A dermoscopic image of a skin lesion: 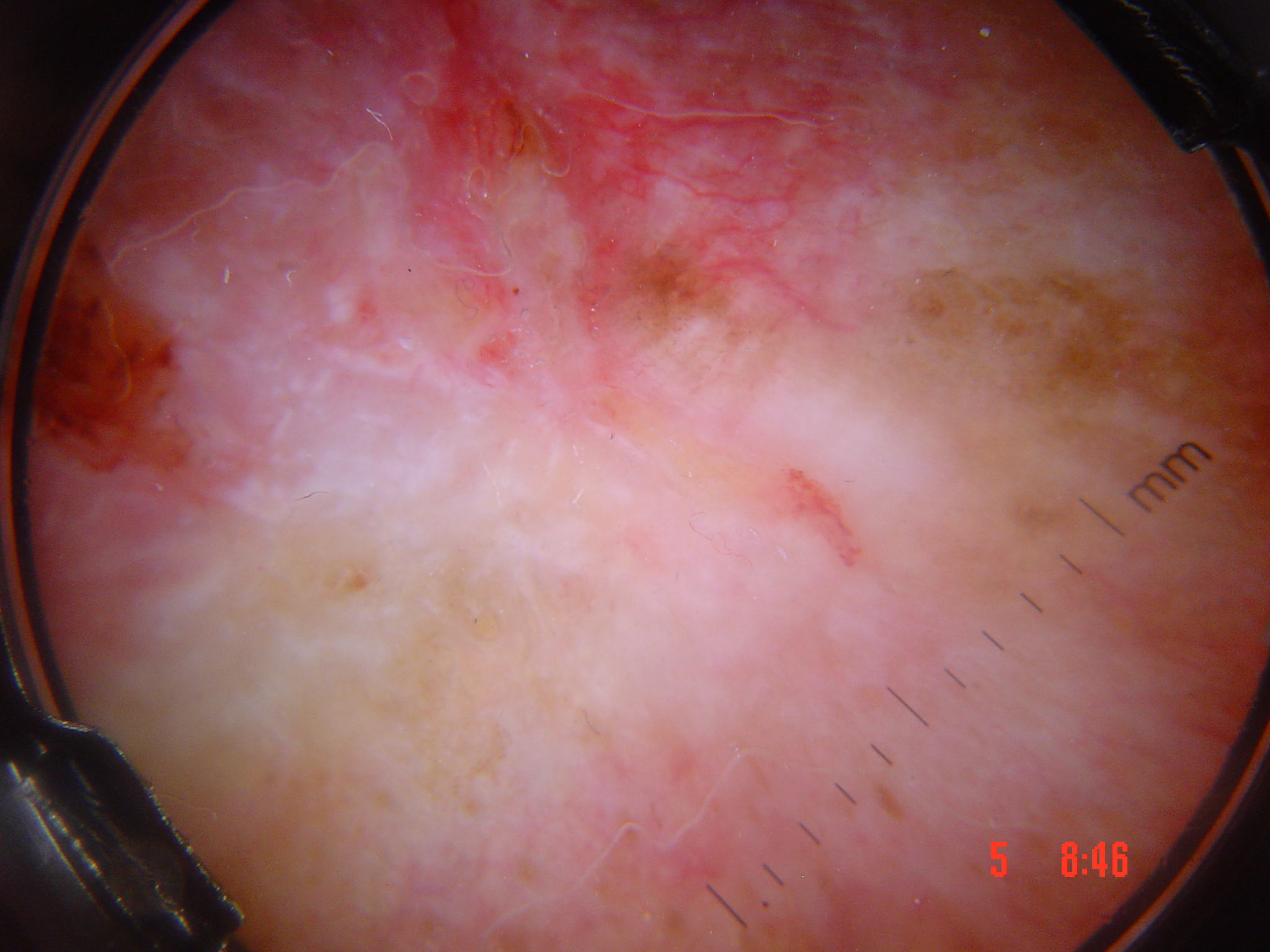diagnosis — squamous cell carcinoma (biopsy-proven).